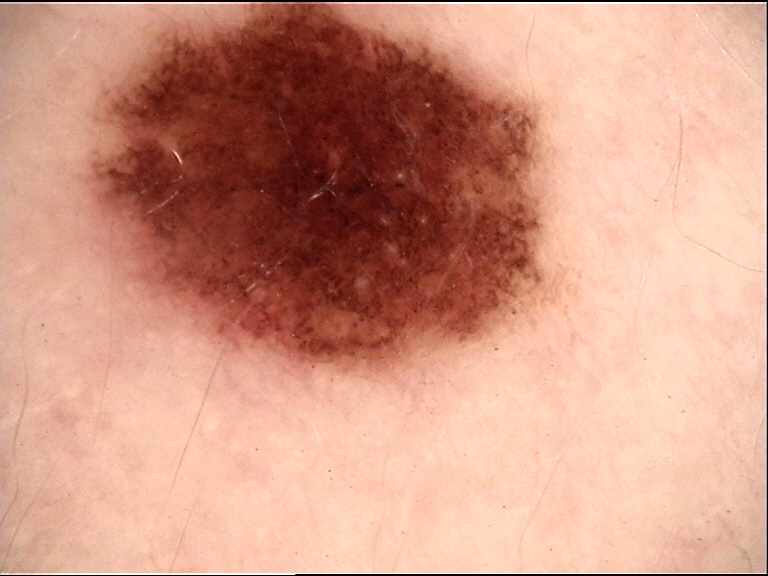Conclusion:
Classified as a benign lesion — a dysplastic compound nevus.